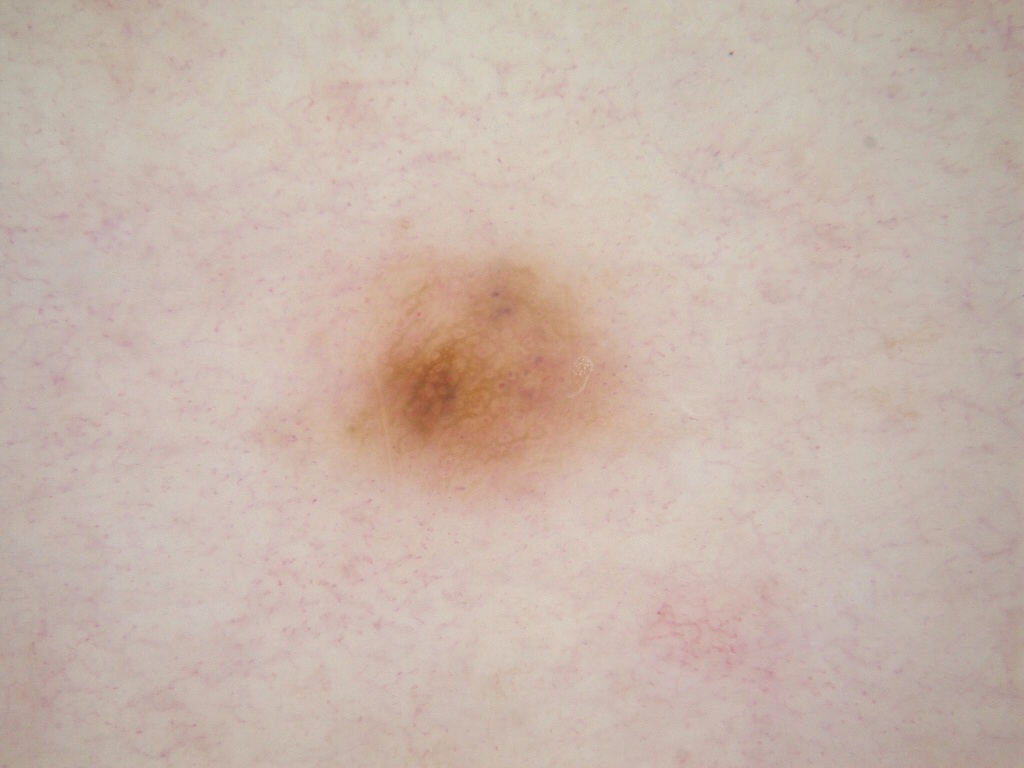A dermoscopic view of a skin lesion. The patient is a female approximately 65 years of age. Dermoscopy demonstrates pigment network and globules, with no negative network, streaks, or milia-like cysts. As (left, top, right, bottom), the lesion spans box(322, 249, 626, 501). Diagnosed as a melanocytic nevus.